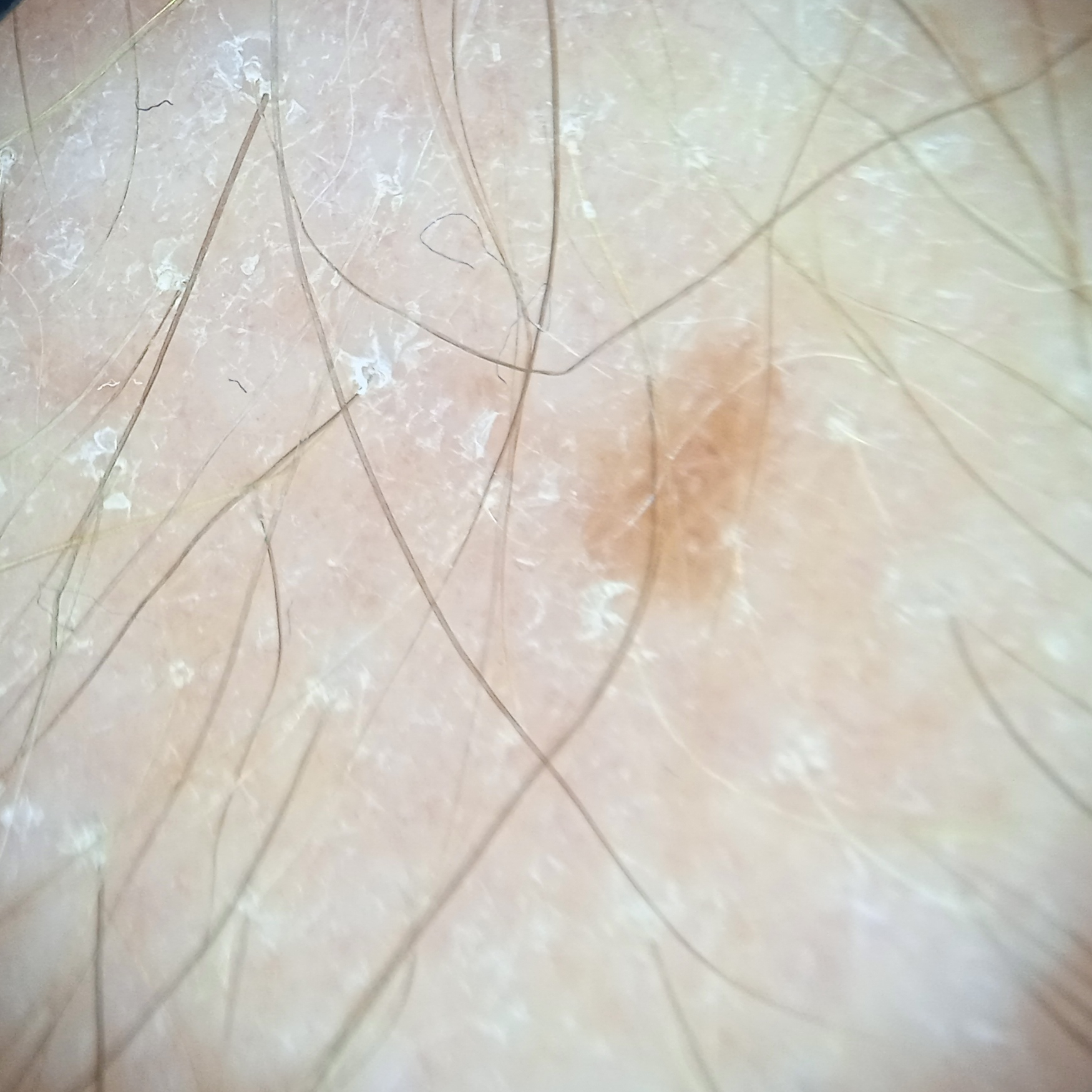A male subject age 66.
A dermoscopy image of a skin lesion.
Imaged for a research study, with no referral diagnosis recorded.
The patient describes having few moles overall.
The patient says their skin reddens with sun exposure.
On a questionnaire the patient reported a prior organ transplant.
The lesion is located on an arm.
The lesion is about 3.4 mm across.
The dermatologists' assessment was a melanocytic nevus.